The subject is a male aged approximately 80. A skin lesion imaged with a dermatoscope — 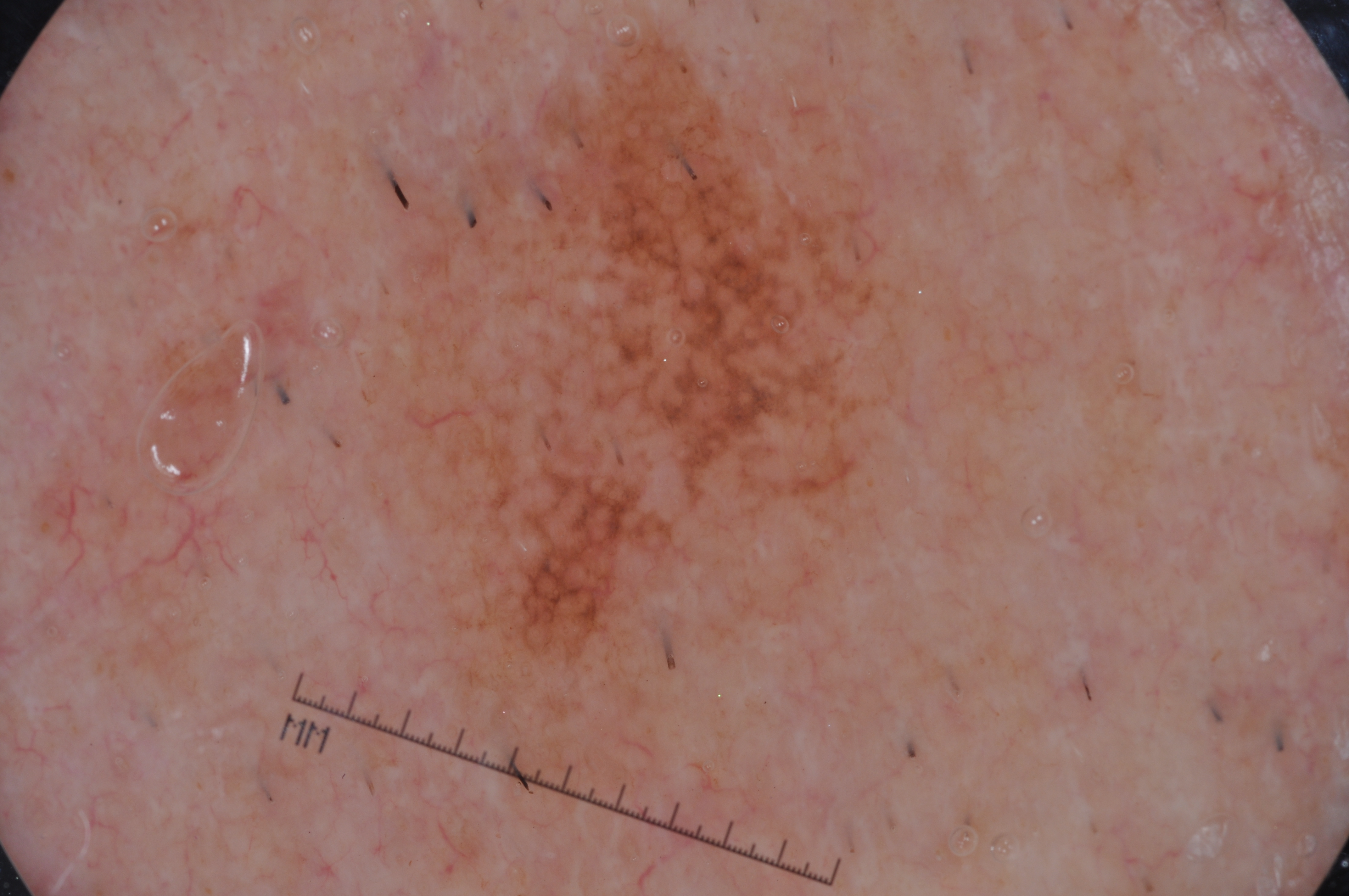As (left, top, right, bottom), lesion location: box(249, 10, 946, 731). Dermoscopically, the lesion shows no streaks, milia-like cysts, negative network, or pigment network. The lesion occupies roughly 31% of the field. Histopathology confirmed a melanoma.